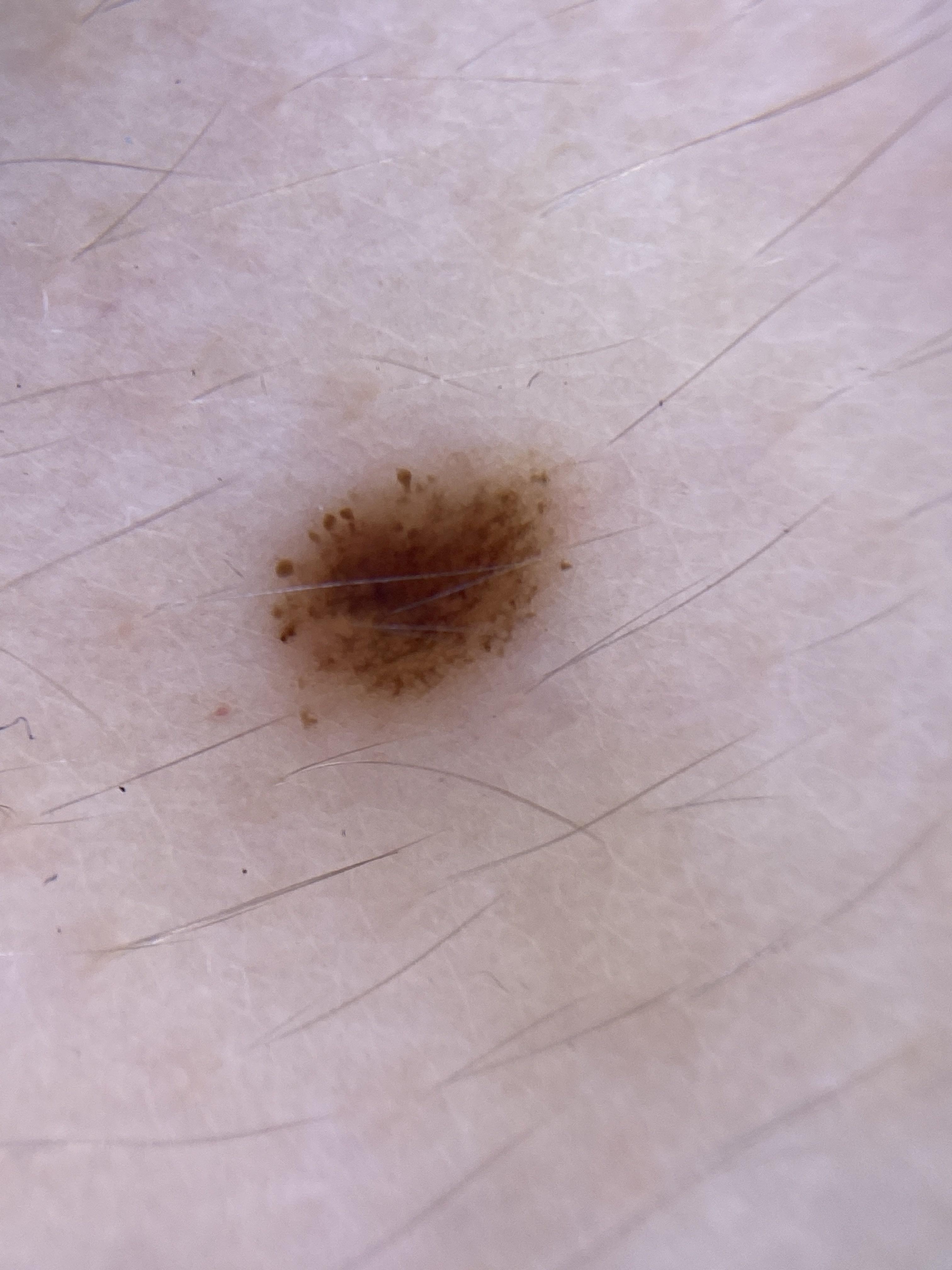Notes:
- location · the trunk (the anterior trunk)
- diagnosis · Nevus (clinical impression)